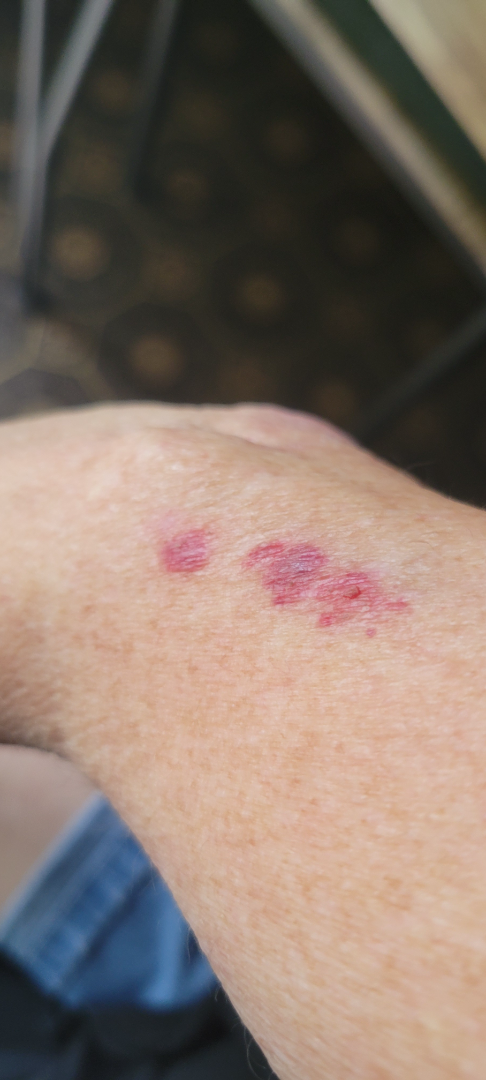Single-reviewer assessment: Abrasion, scrape, or scab and Allergic Contact Dermatitis were considered with similar weight.